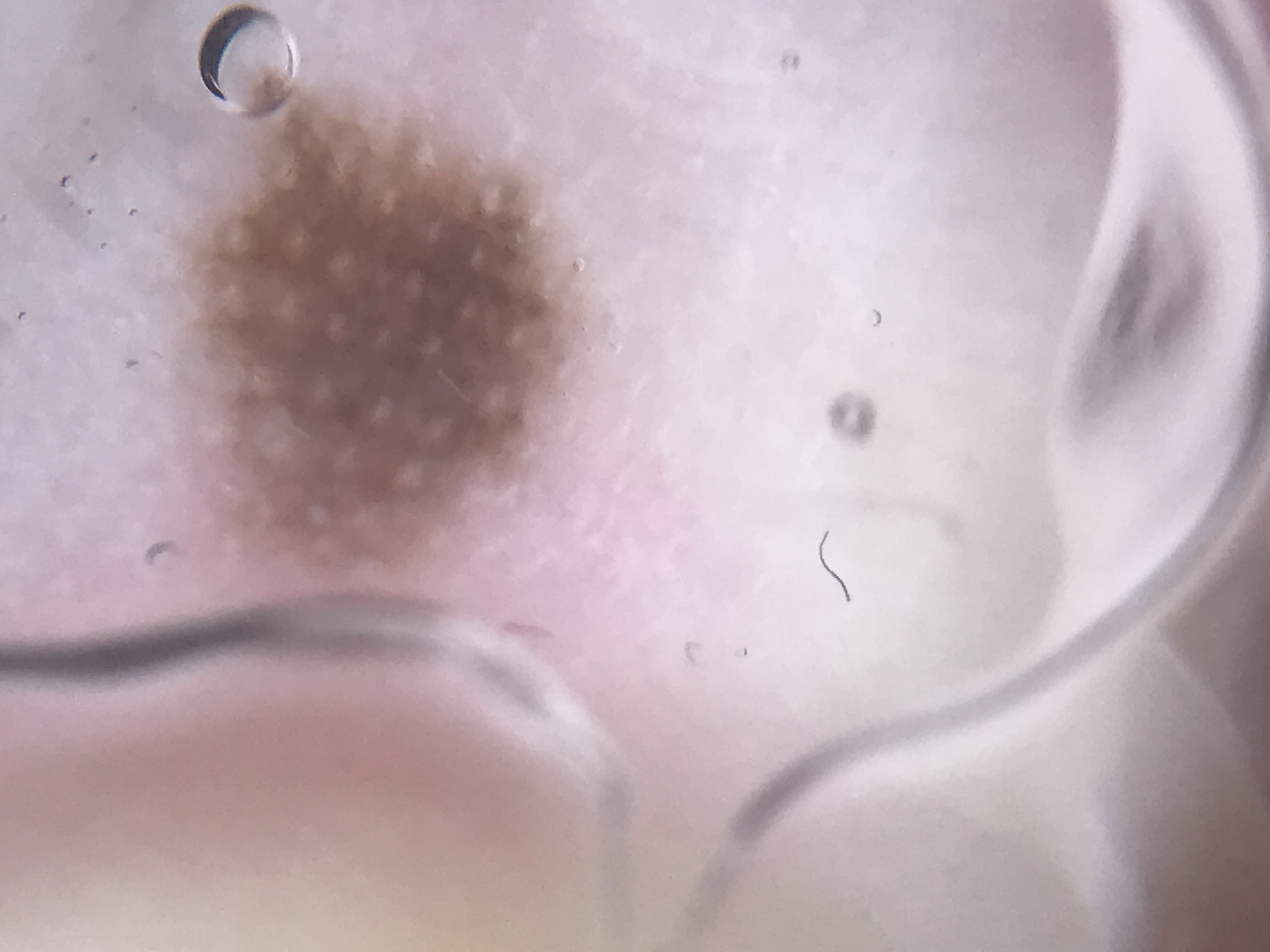Dermoscopy of a skin lesion.
The diagnosis was a banal lesion — an acral junctional nevus.